A dermoscopy image of a single skin lesion.
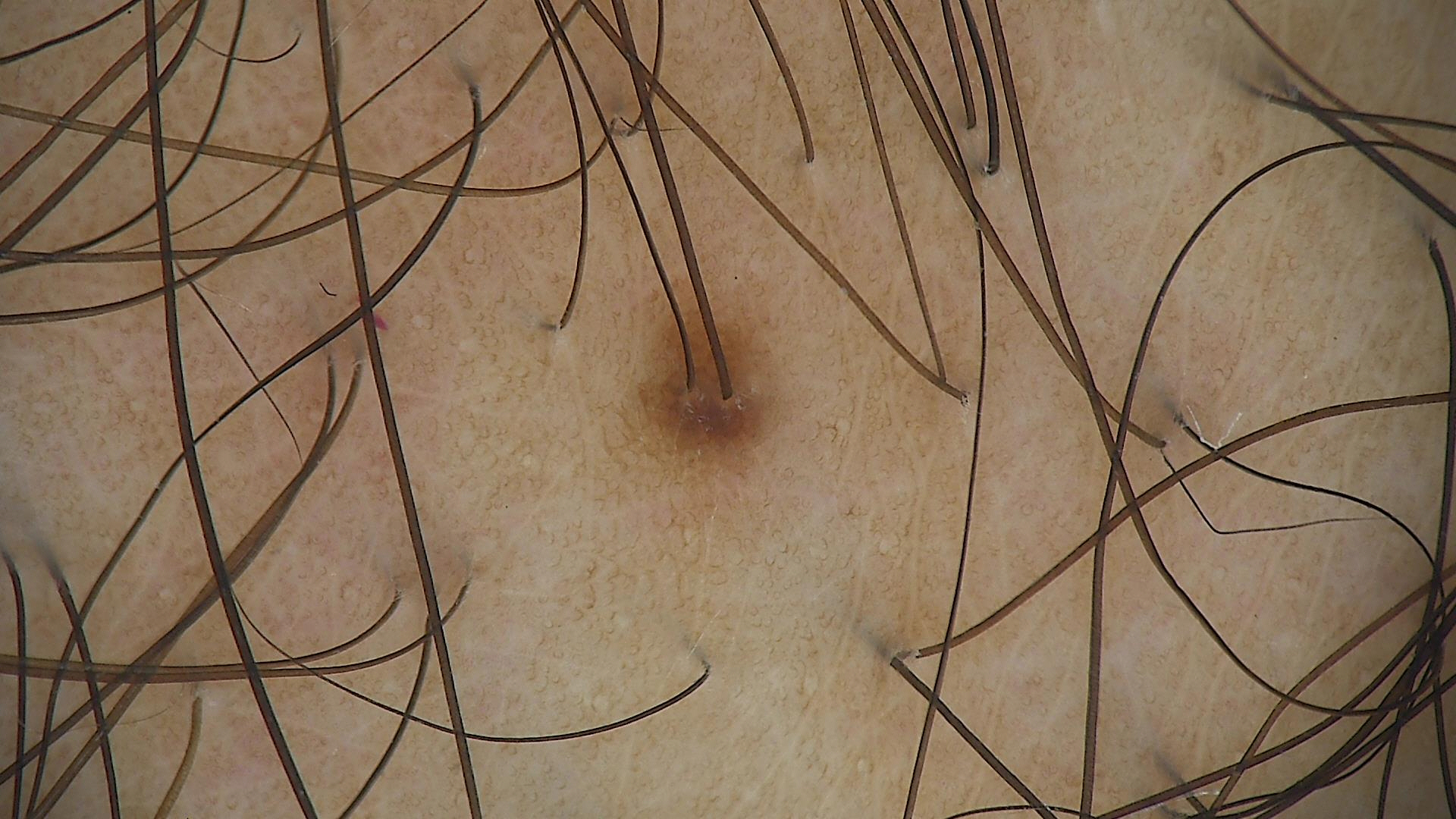Conclusion: Labeled as a dysplastic junctional nevus.